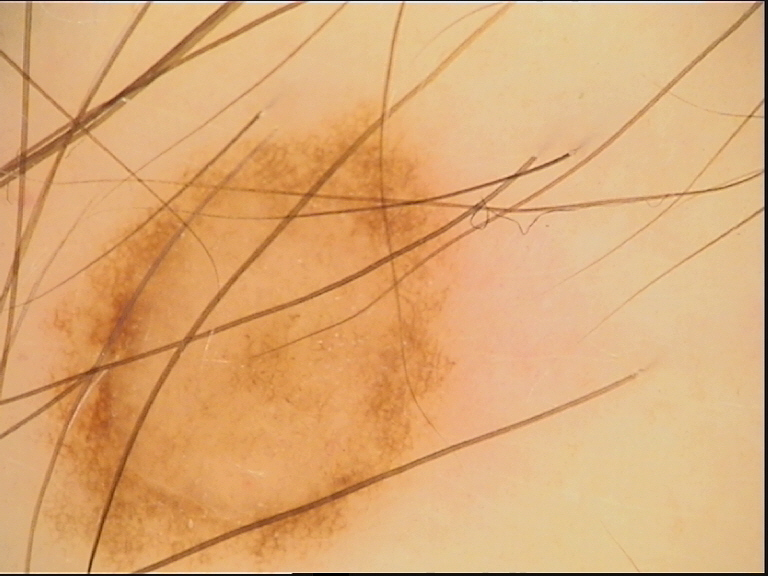imaging — dermatoscopy | class — dysplastic junctional nevus (expert consensus).